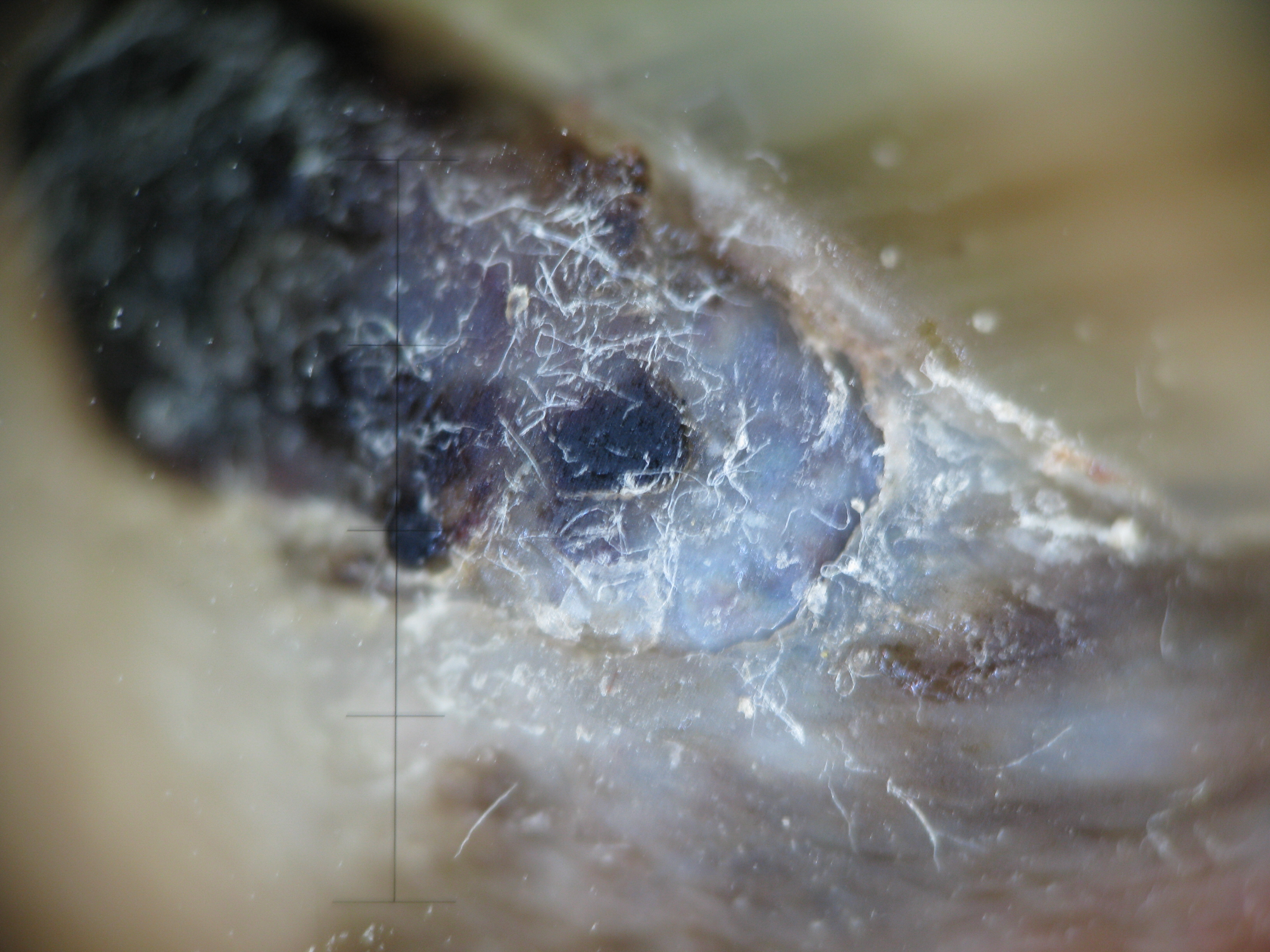Q: What kind of image is this?
A: dermoscopy
Q: What is the diagnosis?
A: acral nodular melanoma (biopsy-proven)